Close-up view. Male subject, age 18–29. The lesion involves the head or neck: 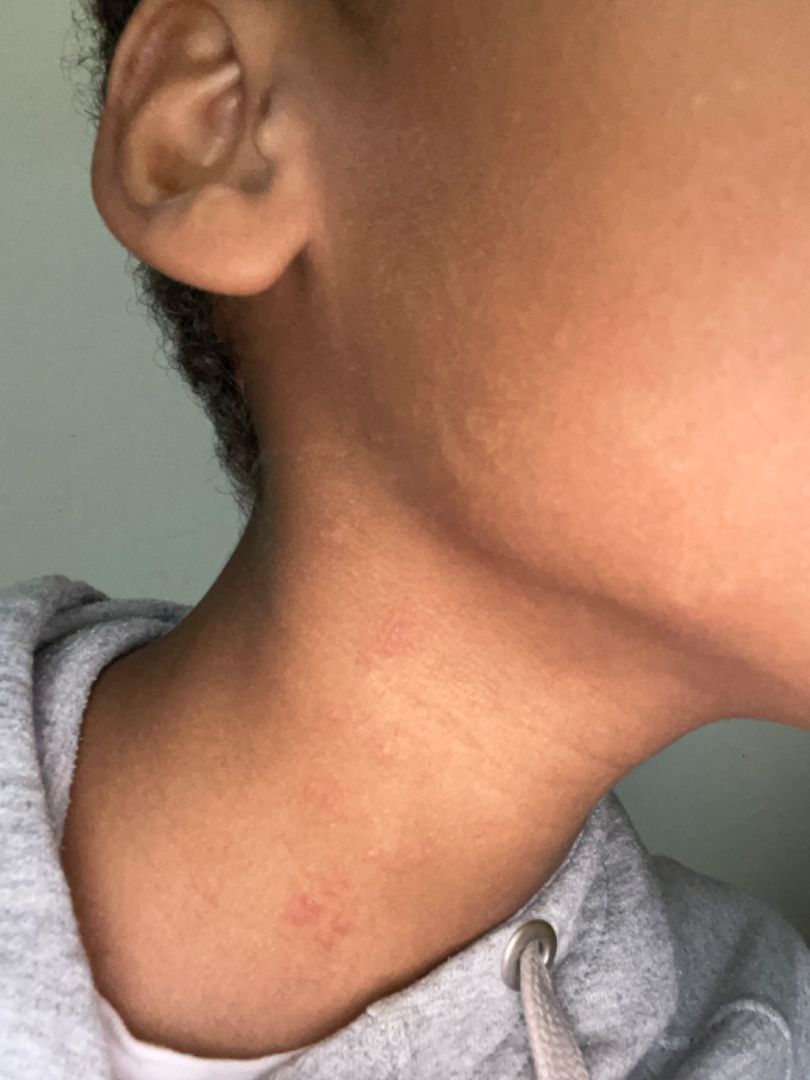Clinical context: The condition has been present for one to four weeks. Reported lesion symptoms include burning and itching. Fitzpatrick skin type V; lay reviewers estimated Monk skin tone scale 4 or 5. Self-categorized by the patient as a rash. The lesion is described as flat and rough or flaky. Assessment: Eczema (54%); Allergic Contact Dermatitis (23%); Irritant Contact Dermatitis (23%).